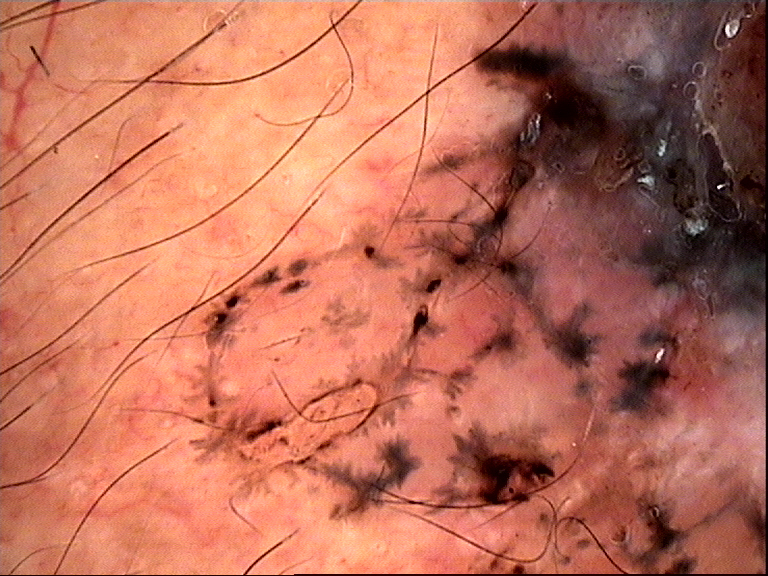label: basal cell carcinoma (biopsy-proven).